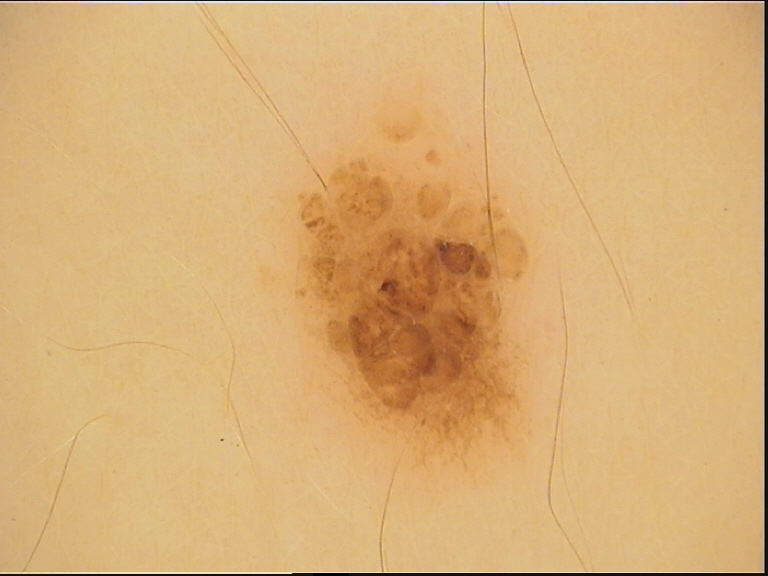A dermoscopic photograph of a skin lesion. Diagnosed as a banal lesion — a compound nevus.